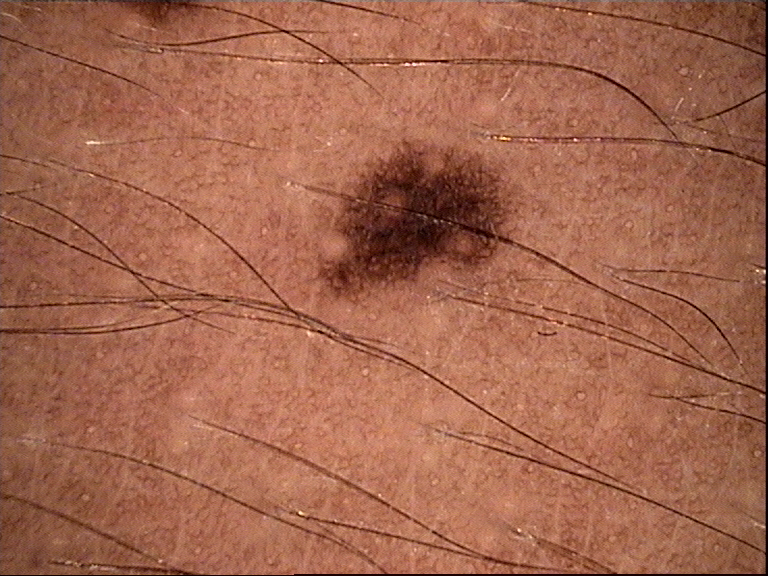<dermoscopy>
<image>dermoscopy</image>
<diagnosis>
<name>dysplastic junctional nevus</name>
<code>jd</code>
<malignancy>benign</malignancy>
<super_class>melanocytic</super_class>
<confirmation>expert consensus</confirmation>
</diagnosis>
</dermoscopy>